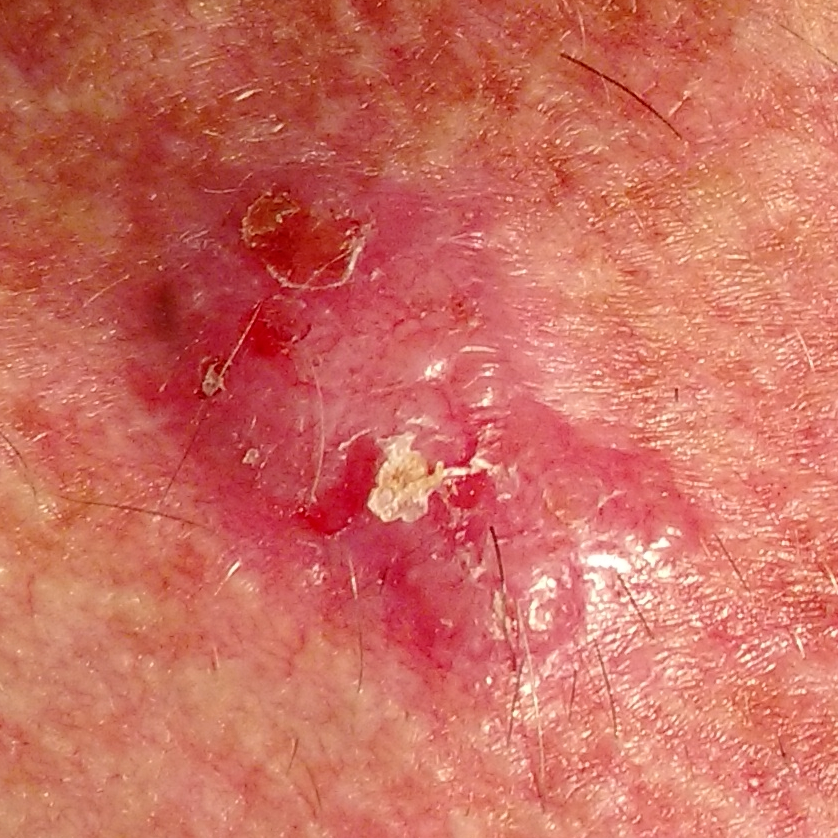Case summary:
The patient is Fitzpatrick II. A male subject 47 years of age. The chart notes pesticide exposure. The lesion was found on the chest. The lesion is roughly 22 by 15 mm. The patient reports that the lesion is elevated, has grown, itches, and has bled.
Conclusion:
The biopsy diagnosis was a skin cancer — a basal cell carcinoma.